A dermoscopic image of a skin lesion · a female subject aged around 80:
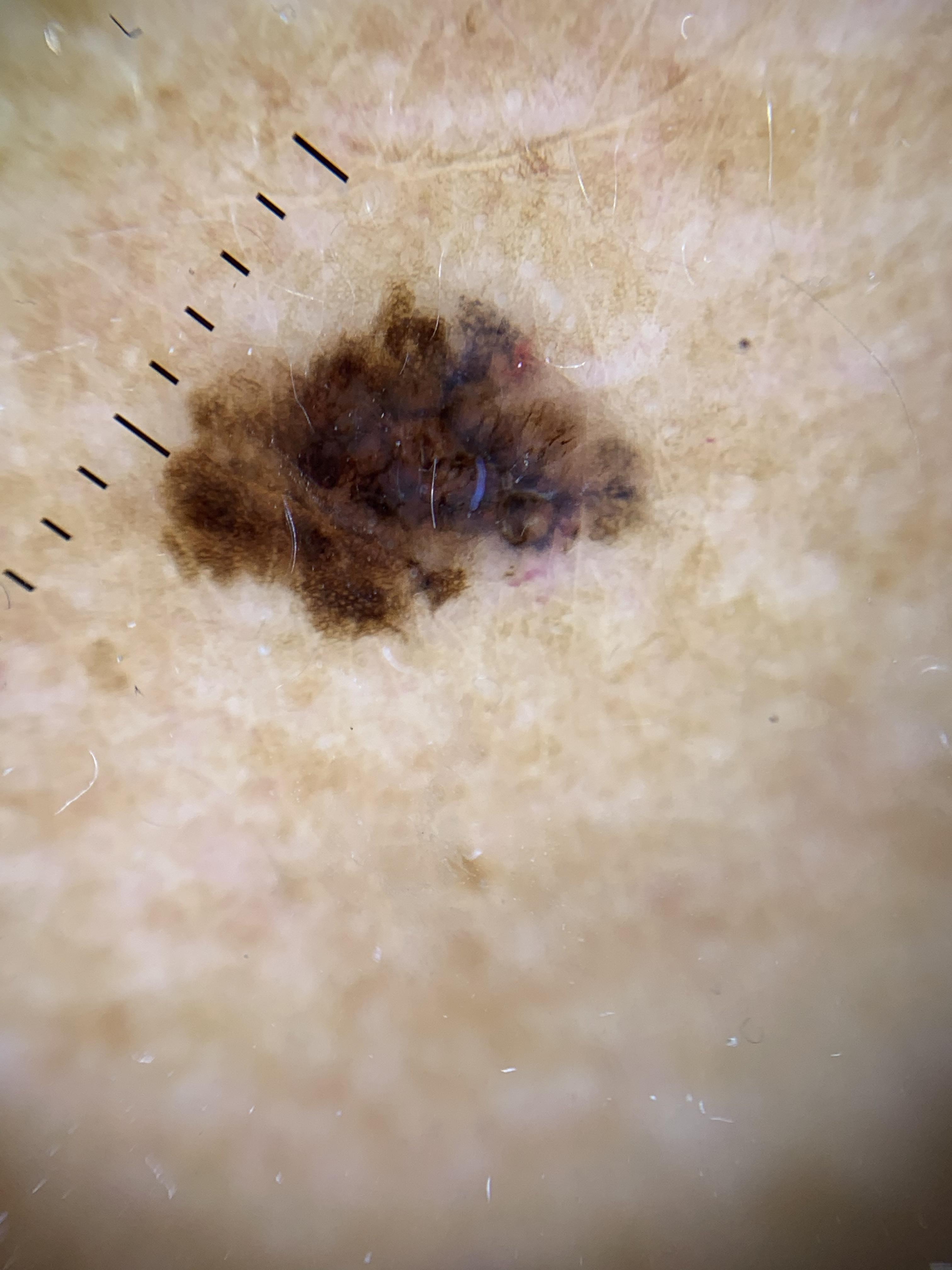Q: Where is the lesion located?
A: the trunk (the posterior trunk)
Q: What is the diagnosis?
A: Melanoma (biopsy-proven)